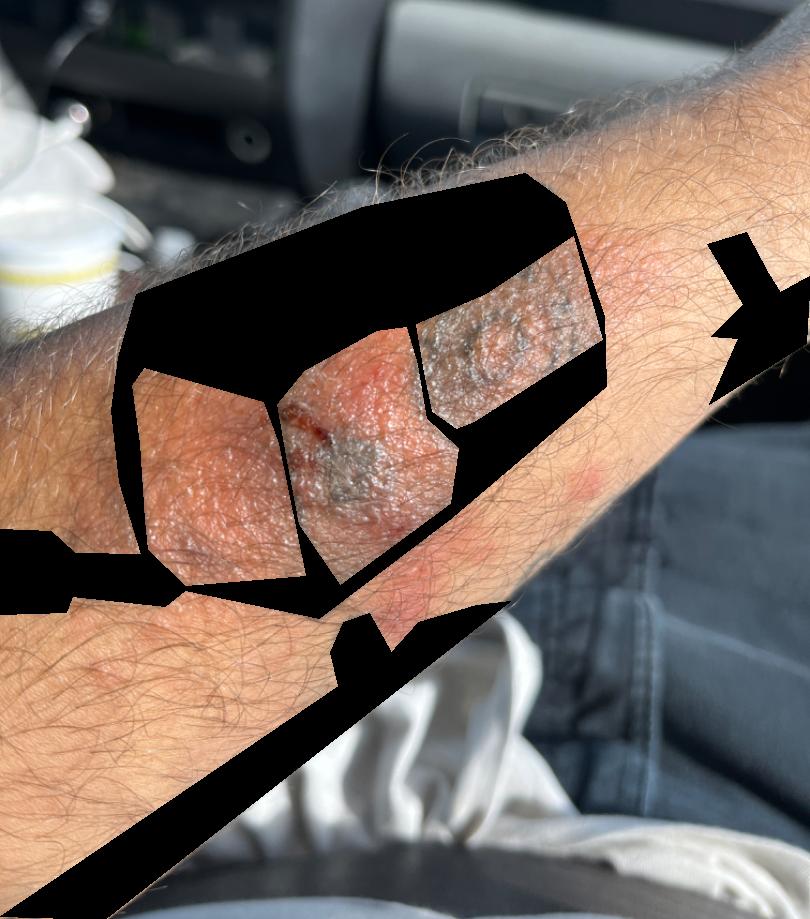Findings:
The reviewing dermatologist was unable to assign a differential diagnosis from the image.
Background:
Texture is reported as raised or bumpy and fluid-filled. The affected area is the arm. This is a close-up image. The contributor reports itching, enlargement and bothersome appearance. Reported duration is less than one week.